A dermatoscopic image of a skin lesion.
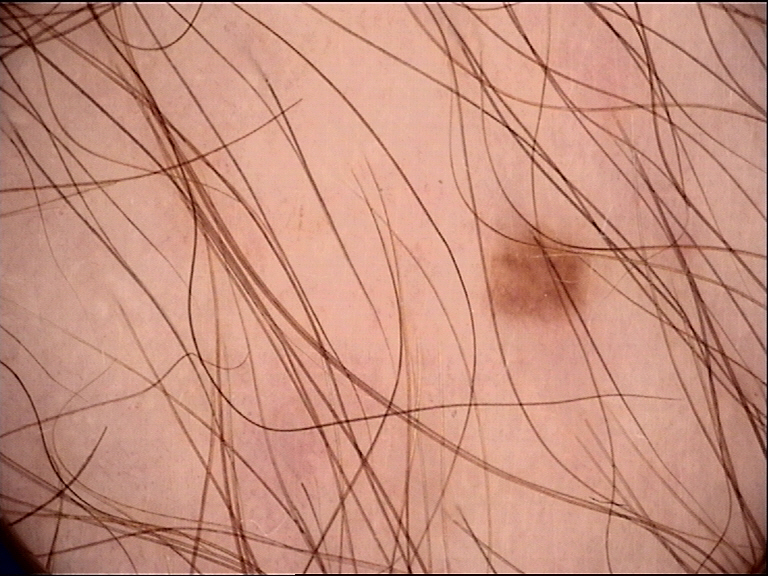lesion type = banal; diagnostic label = junctional nevus (expert consensus).